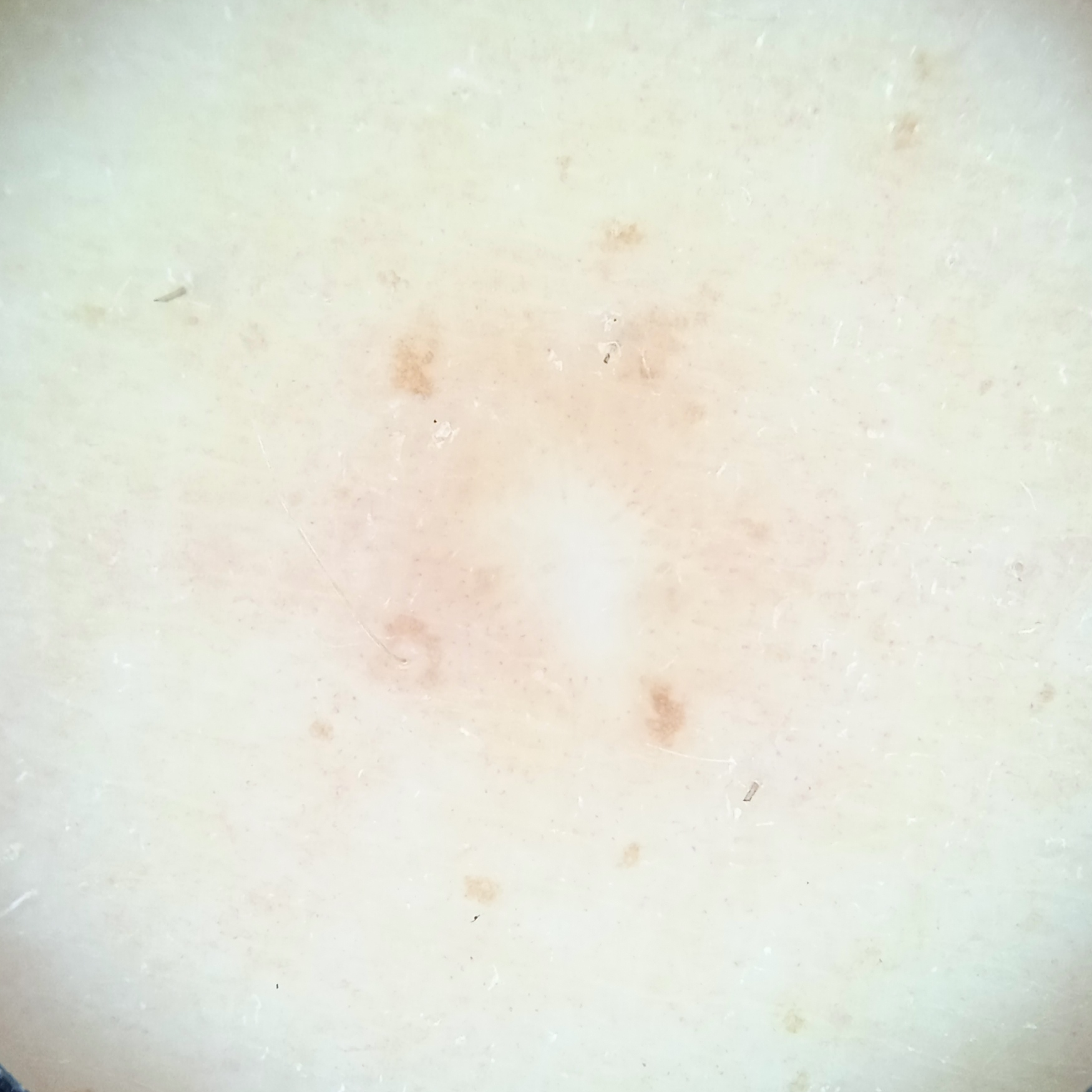subject — female, 32 years of age | referral context — research study (no referral diagnosis) | nevus count — a moderate number of melanocytic nevi | sun reaction — skin reddens with sun exposure | relevant history — a personal history of skin cancer, a personal history of cancer, no immunosuppression, no prior organ transplant | image — dermoscopy | anatomic site — a leg | diameter — 5.4 mm | assessment — dermatofibroma (dermatologist consensus).